The lesion involves the leg. The subject is a female aged 70–79. The photograph was taken at a distance: 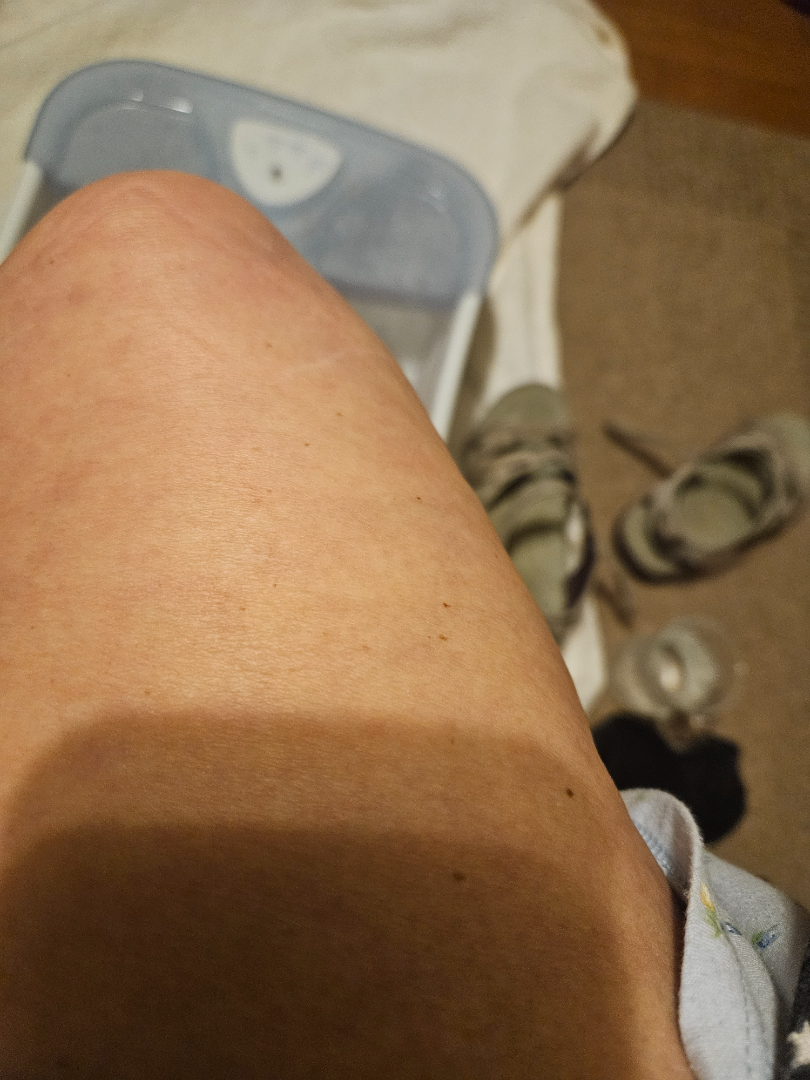Findings: No skin condition was discernible on photographic review. Background: The patient considered this a rash. FST III; lay graders estimated Monk skin tone scale 3–4. Present for one to three months.